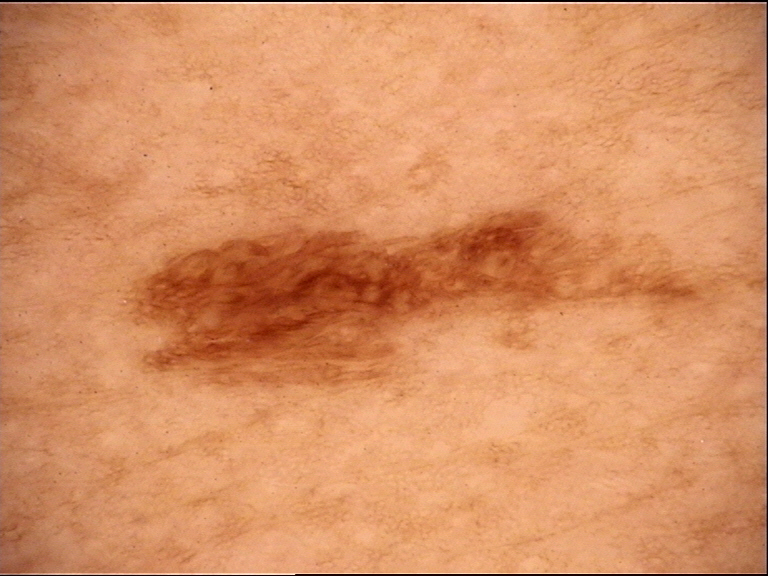Q: What is this lesion?
A: seborrheic keratosis (expert consensus)